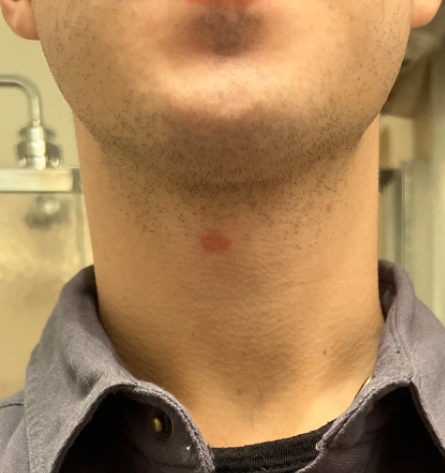view — at a distance
dermatologist impression — the differential, in no particular order, includes Skin and soft tissue atypical mycobacterial infection and Basal Cell Carcinoma; less probable is Pityriasis rosea